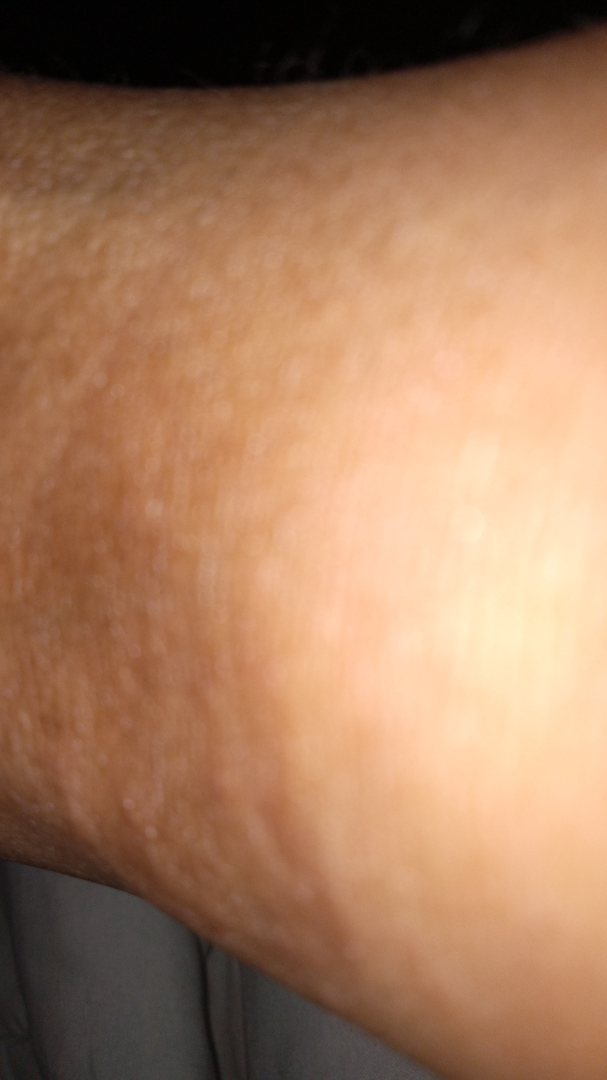The condition could not be reliably identified from the image.
The affected area is the arm.
Skin tone: lay reviewers estimated 4 on the Monk skin tone scale.
Close-up view.
No relevant systemic symptoms.
The lesion is described as raised or bumpy.
Present for less than one week.
The contributor is a female aged 50–59.